The photo was captured at an angle — 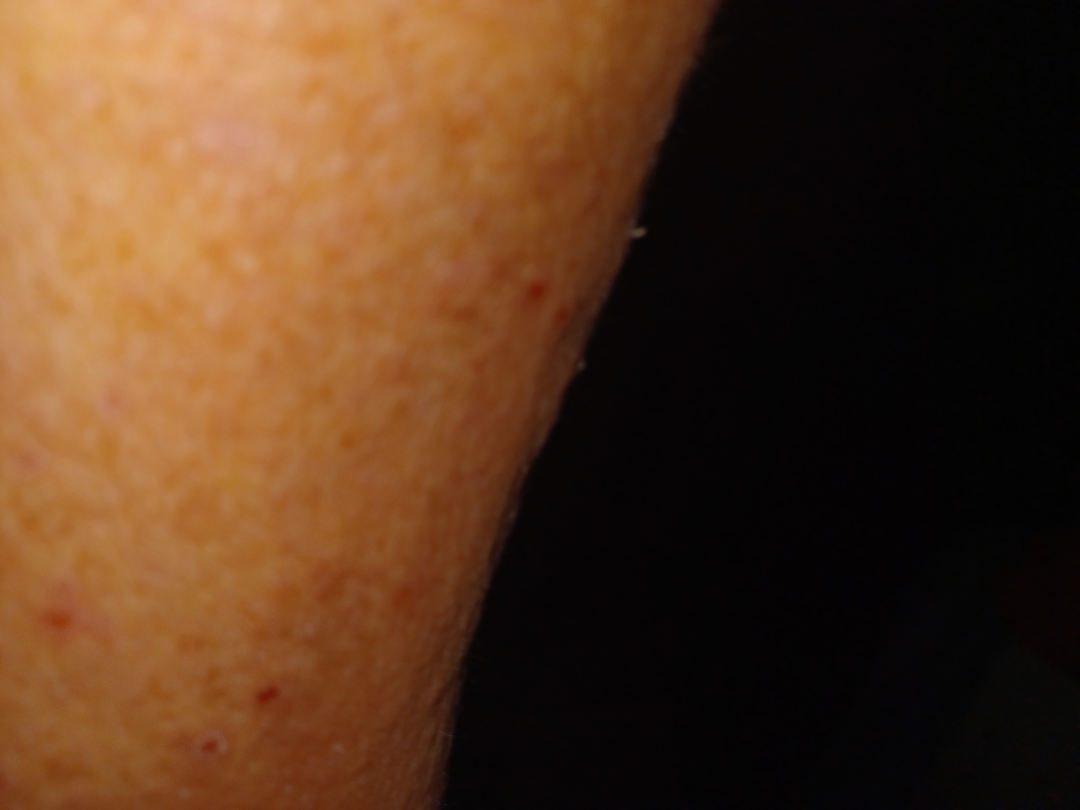The reviewer was unable to grade this case for skin condition.